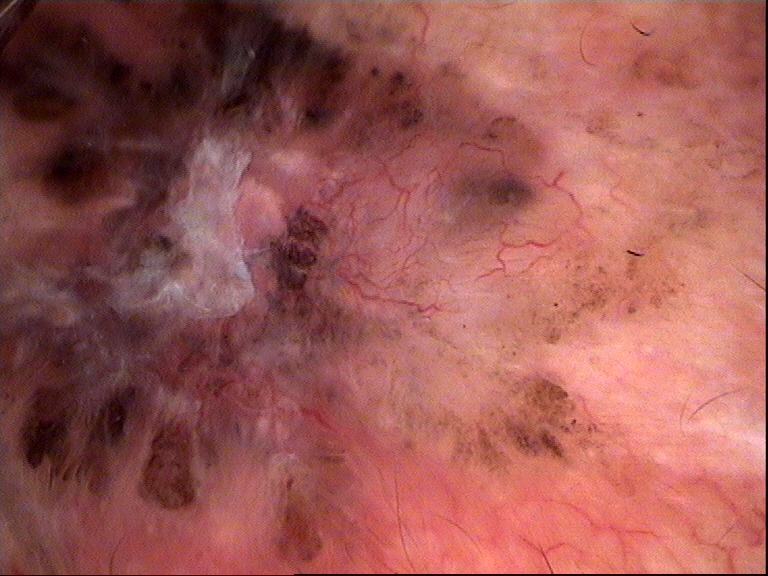{
  "lesion_type": {
    "main_class": "keratinocytic"
  },
  "diagnosis": {
    "name": "basal cell carcinoma",
    "code": "bcc",
    "malignancy": "malignant",
    "super_class": "non-melanocytic",
    "confirmation": "histopathology"
  }
}